The lesion is associated with itching. The lesion is described as fluid-filled. The patient reported no systemic symptoms. Skin tone: FST IV; non-clinician graders estimated Monk Skin Tone 5 (US pool) or 4 (India pool). The patient is a female aged 60–69. This image was taken at an angle.
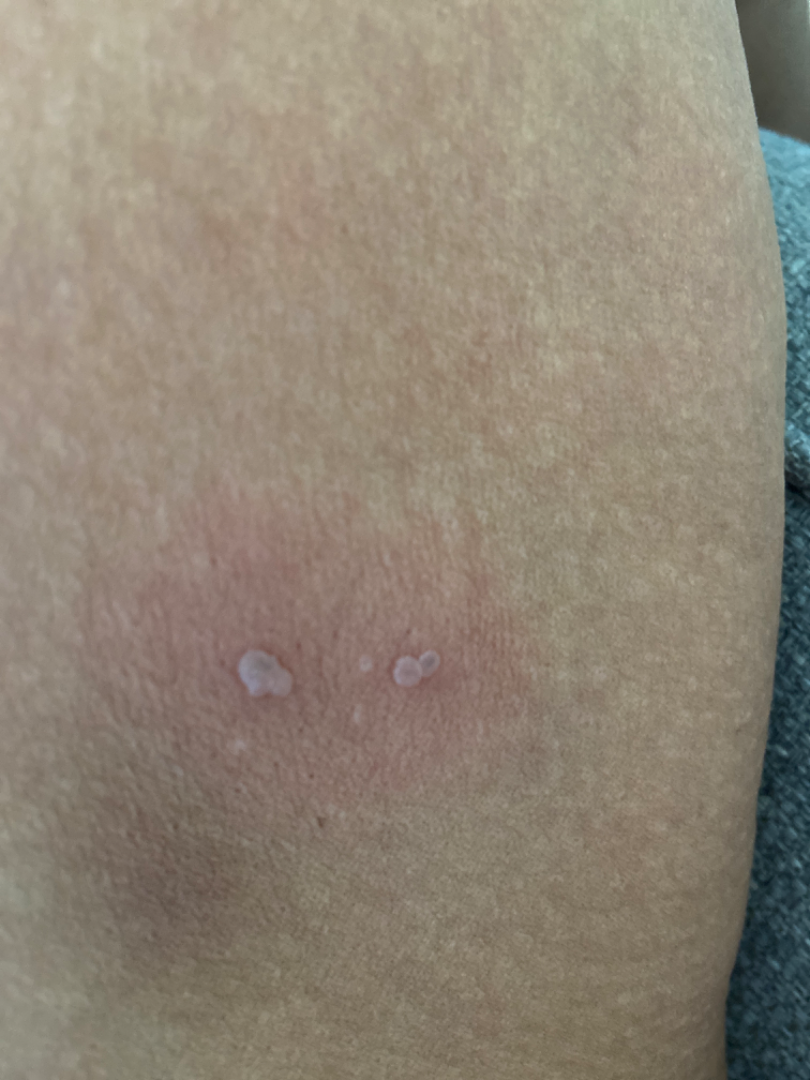Most likely Herpes Simplex; the differential also includes Impetigo; also raised was Herpes Zoster.